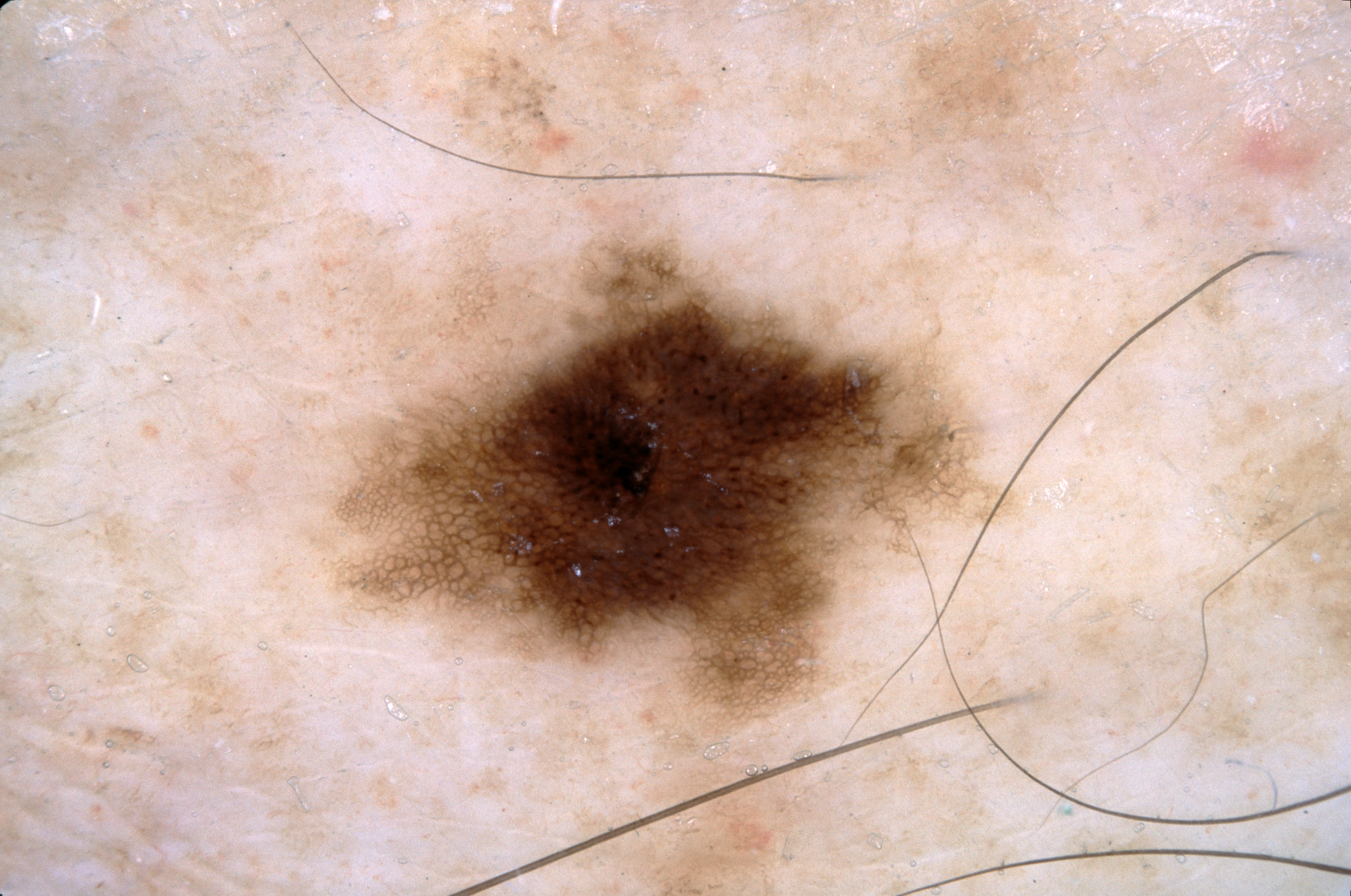  image:
    modality: dermoscopy
  lesion_location:
    bbox_xyxy:
      - 348
      - 245
      - 961
      - 707
  diagnosis:
    name: melanocytic nevus
    malignancy: benign
    lineage: melanocytic
    provenance: clinical